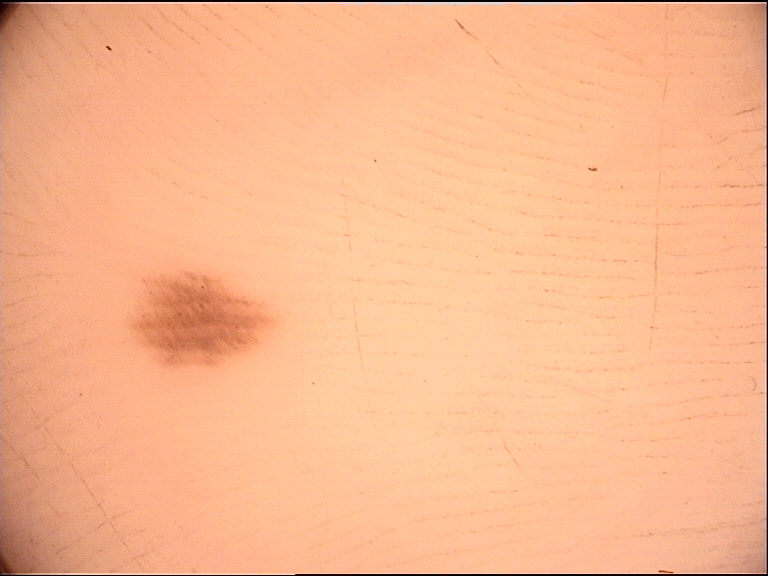Impression:
The diagnostic label was a benign lesion — an acral dysplastic junctional nevus.